A dermatoscopic image of a skin lesion:
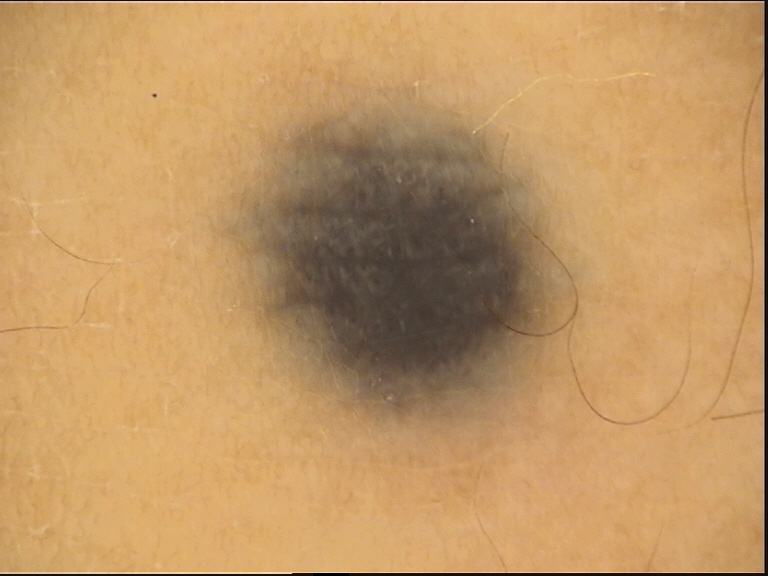Classified as a banal lesion — a blue nevus.